A skin lesion imaged with a dermatoscope: 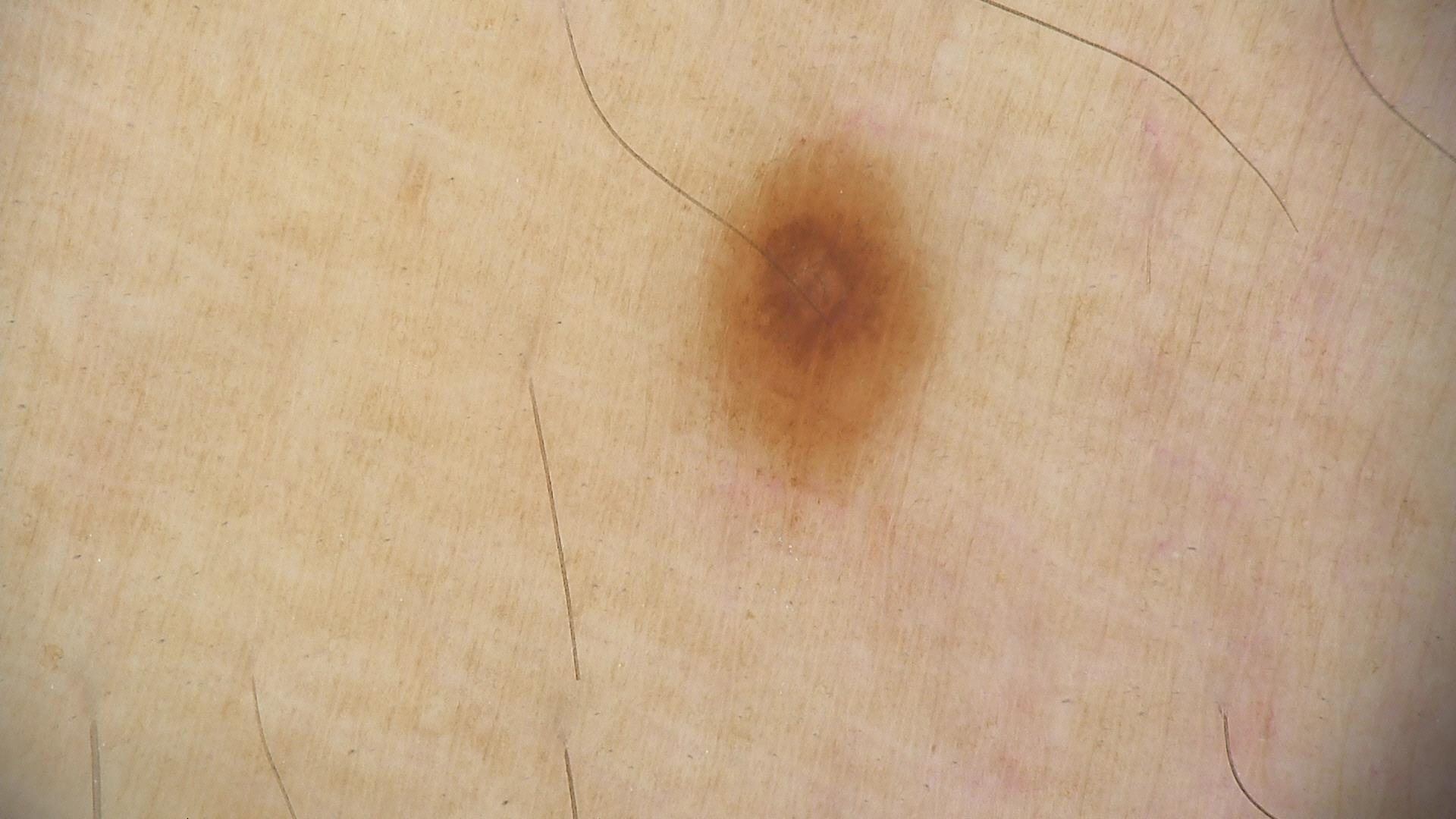{
  "diagnosis": {
    "name": "dysplastic junctional nevus",
    "code": "jd",
    "malignancy": "benign",
    "super_class": "melanocytic",
    "confirmation": "expert consensus"
  }
}